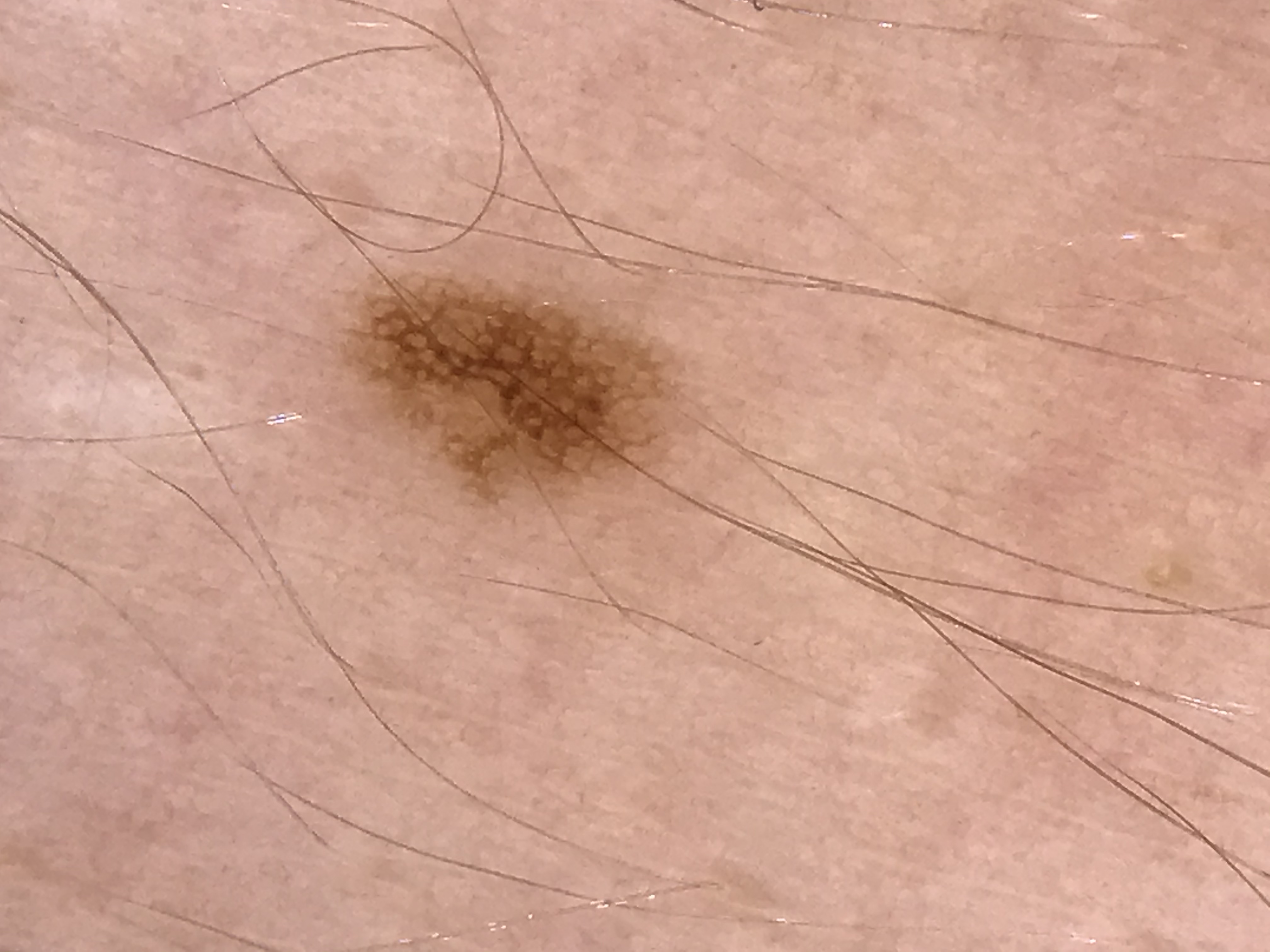Summary:
A skin lesion imaged with a dermatoscope.
Conclusion:
Labeled as a dysplastic junctional nevus.